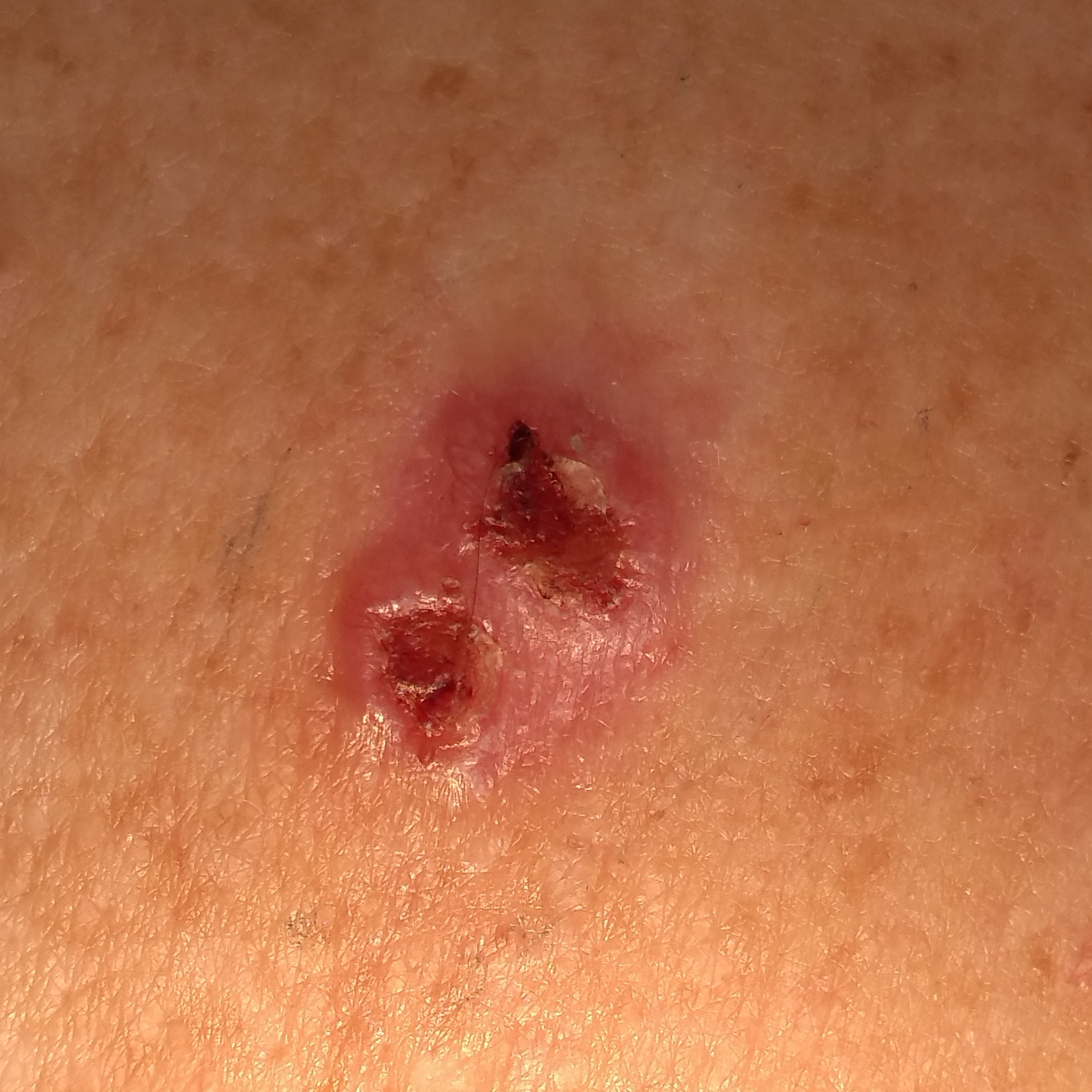A female patient 55 years of age. The patient reports that the lesion is elevated, itches, has bled, and has grown, but does not hurt. Histopathological examination showed a basal cell carcinoma.